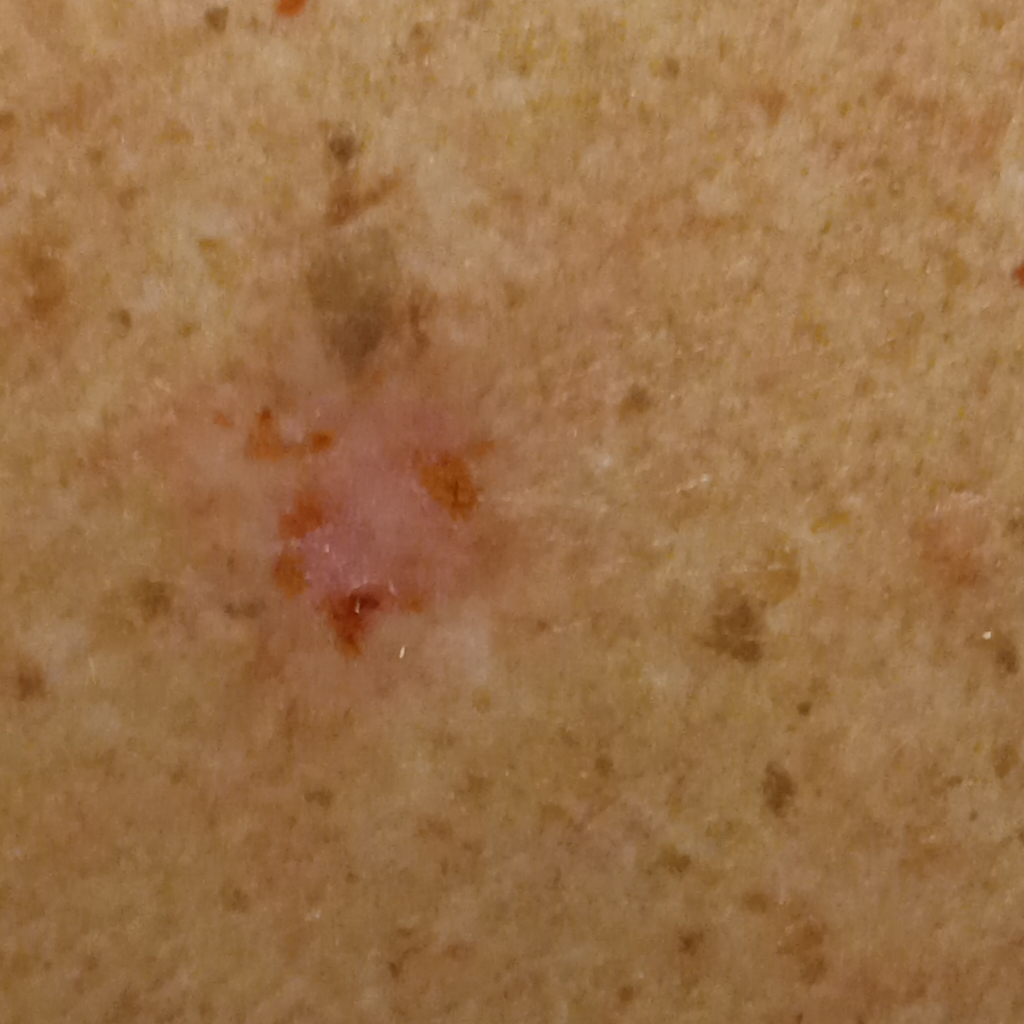A clinical close-up of a skin lesion. A male patient aged 81. The patient says their skin reddens with sun exposure. By self-report, a personal history of cancer, a family history of skin cancer, no personal history of skin cancer, and no prior organ transplant. The patient describes having few moles overall. Referred for assessment of suspected basal cell carcinoma. The lesion is on the back. The lesion measures approximately 12.6 mm. On biopsy, the diagnosis was a basal cell carcinoma, following excision, with a measured thickness of 3 mm.